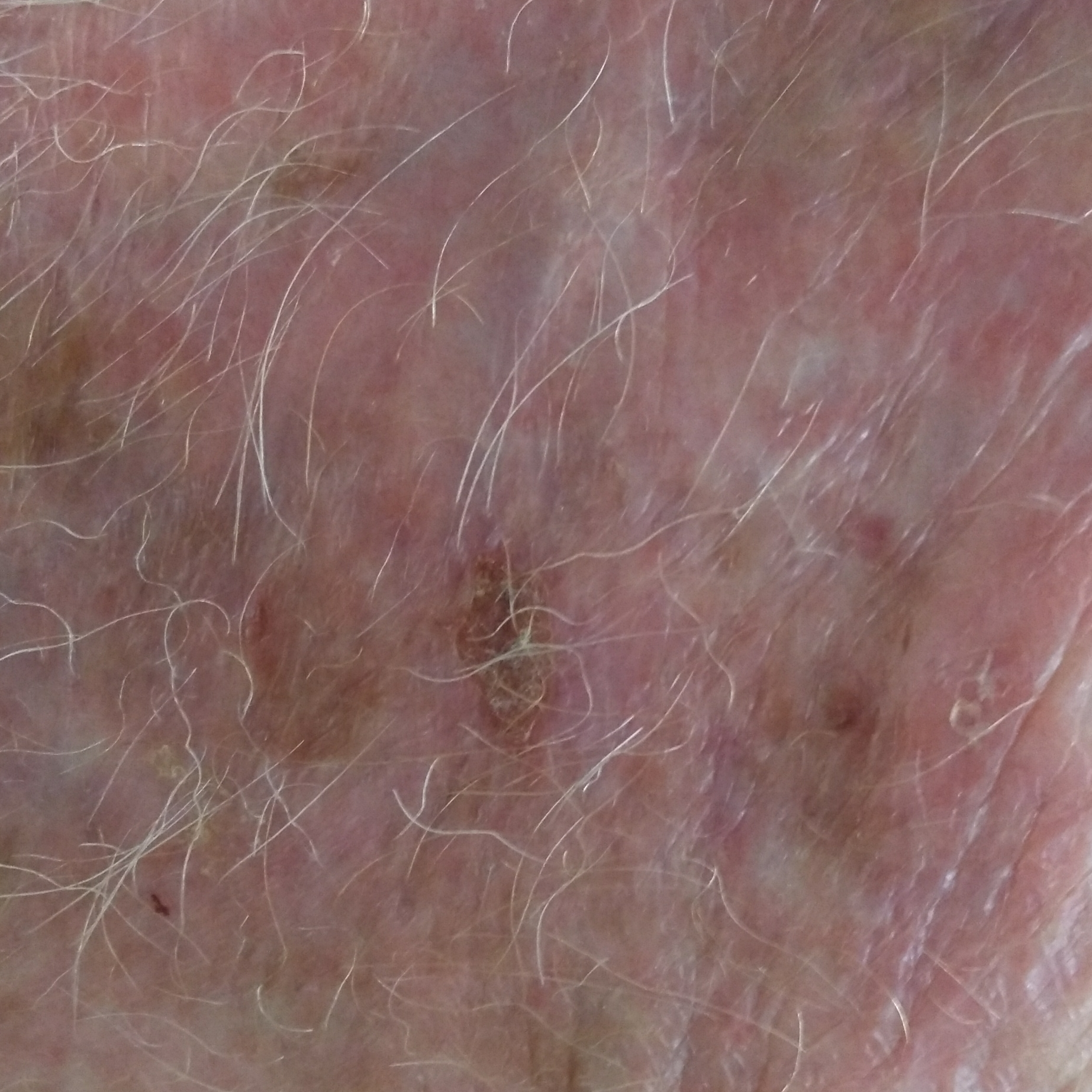Clinical context:
A clinical photograph showing a skin lesion. The lesion is on a hand.
Conclusion:
Consistent with an actinic keratosis.